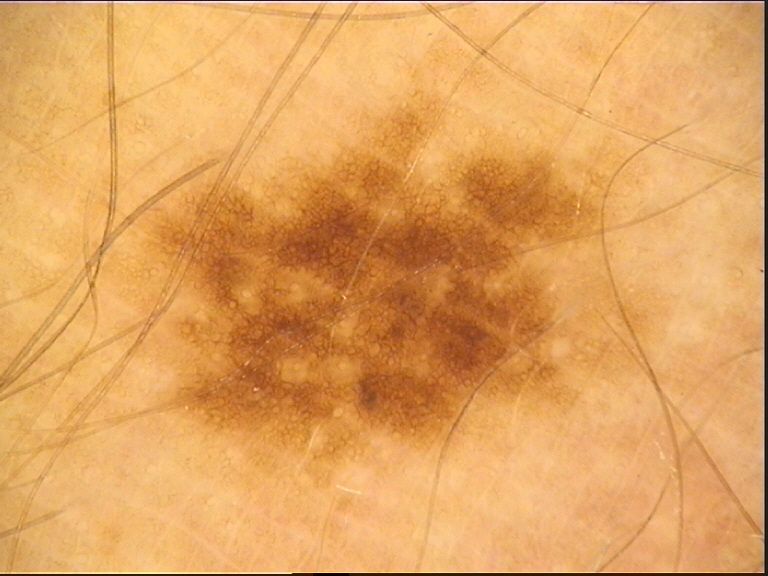| feature | finding |
|---|---|
| diagnostic label | dysplastic junctional nevus (expert consensus) |